A skin lesion imaged with a dermatoscope: 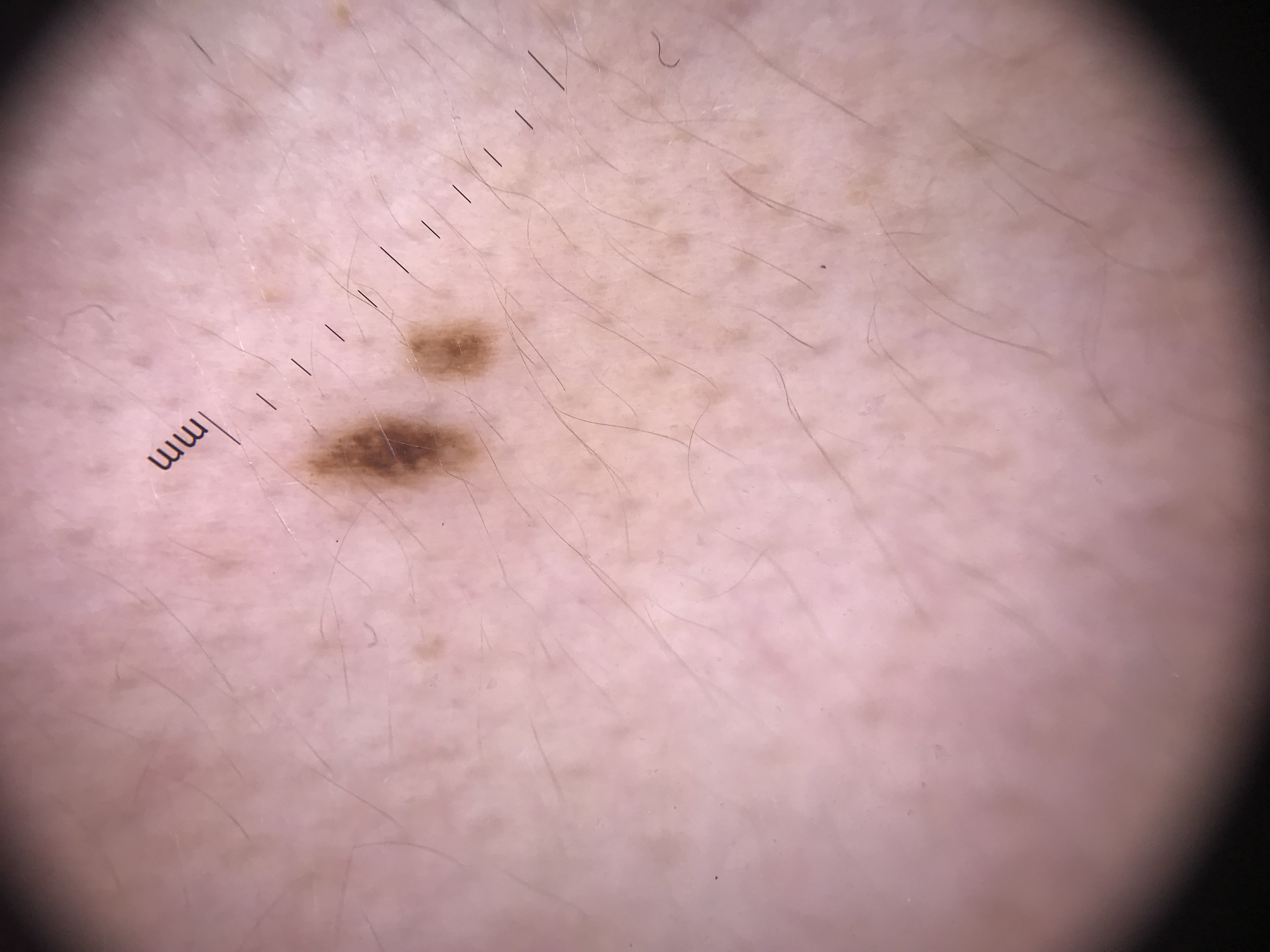The diagnostic label was a benign lesion — a dysplastic junctional nevus.